A dermoscopic close-up of a skin lesion: 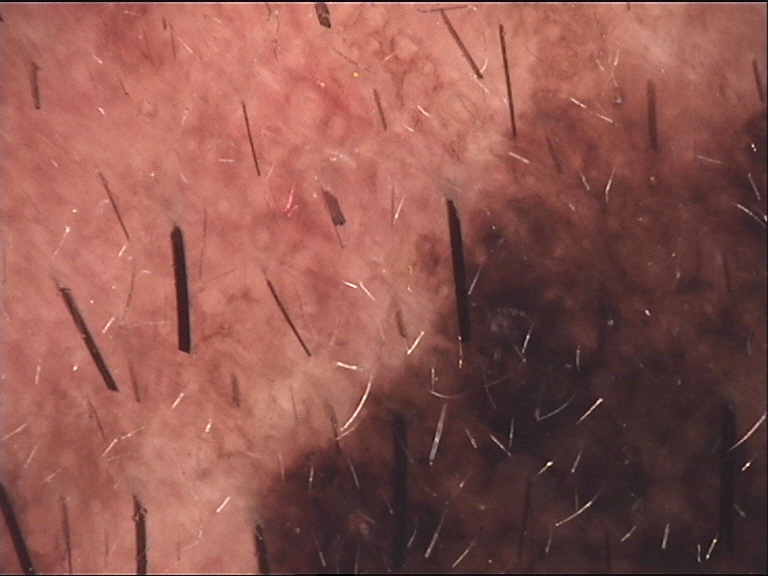Conclusion:
The diagnostic label was a banal lesion — a congenital compound nevus.